A dermoscopic close-up of a skin lesion — 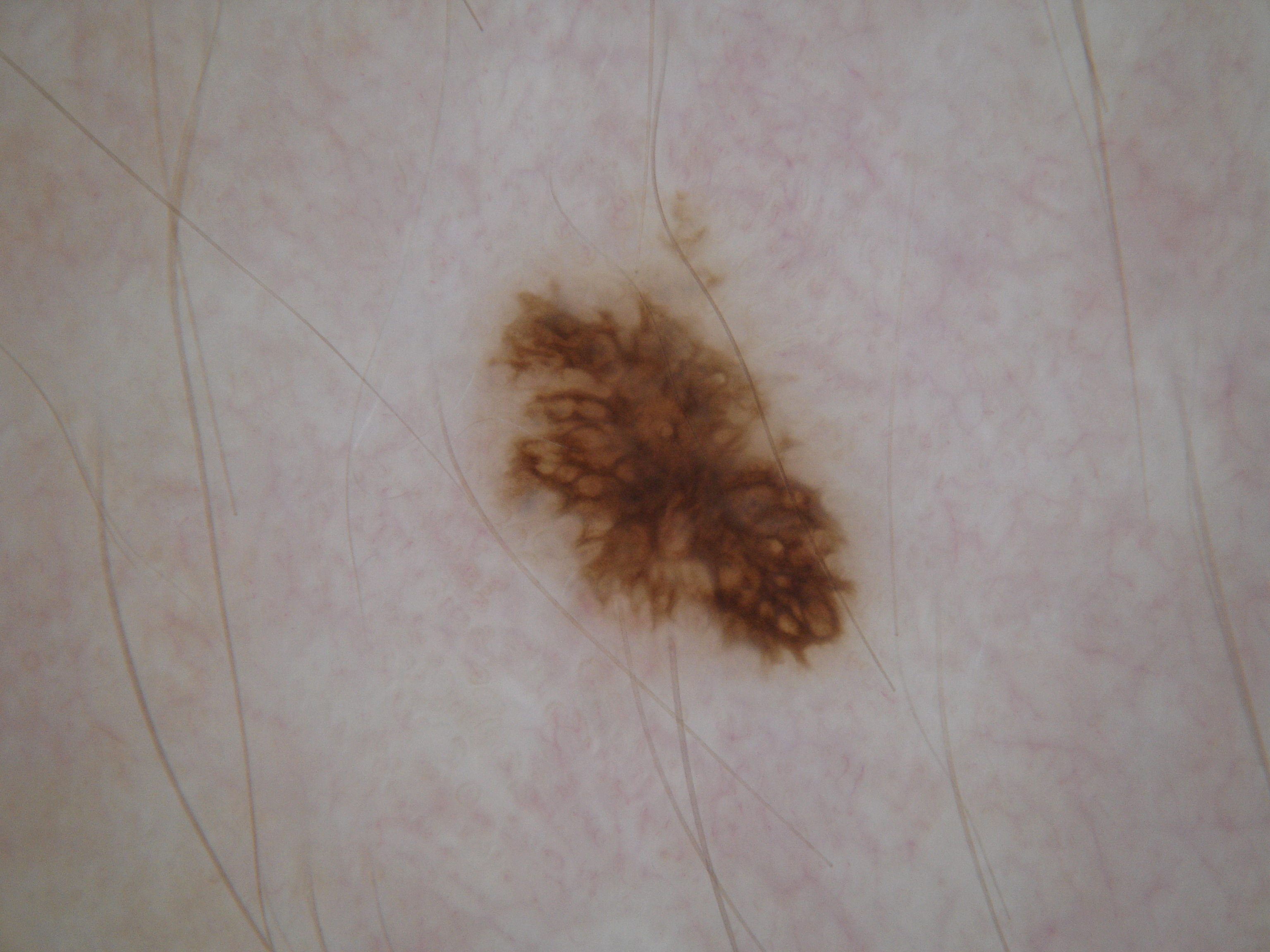Dermoscopic review identifies pigment network, with no streaks, milia-like cysts, negative network, or globules.
With coordinates (x1, y1, x2, y2), the visible lesion spans [467,169,868,690].
Clinically diagnosed as a melanocytic nevus.